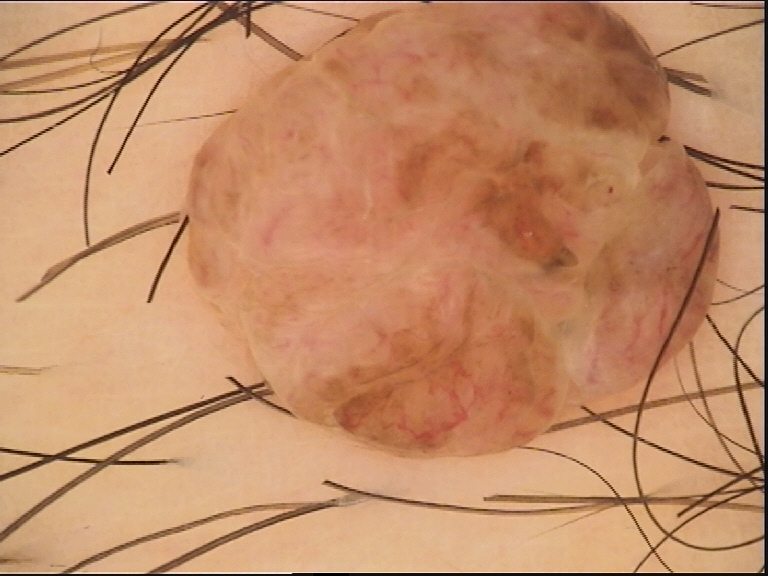class=dermal nevus (expert consensus).